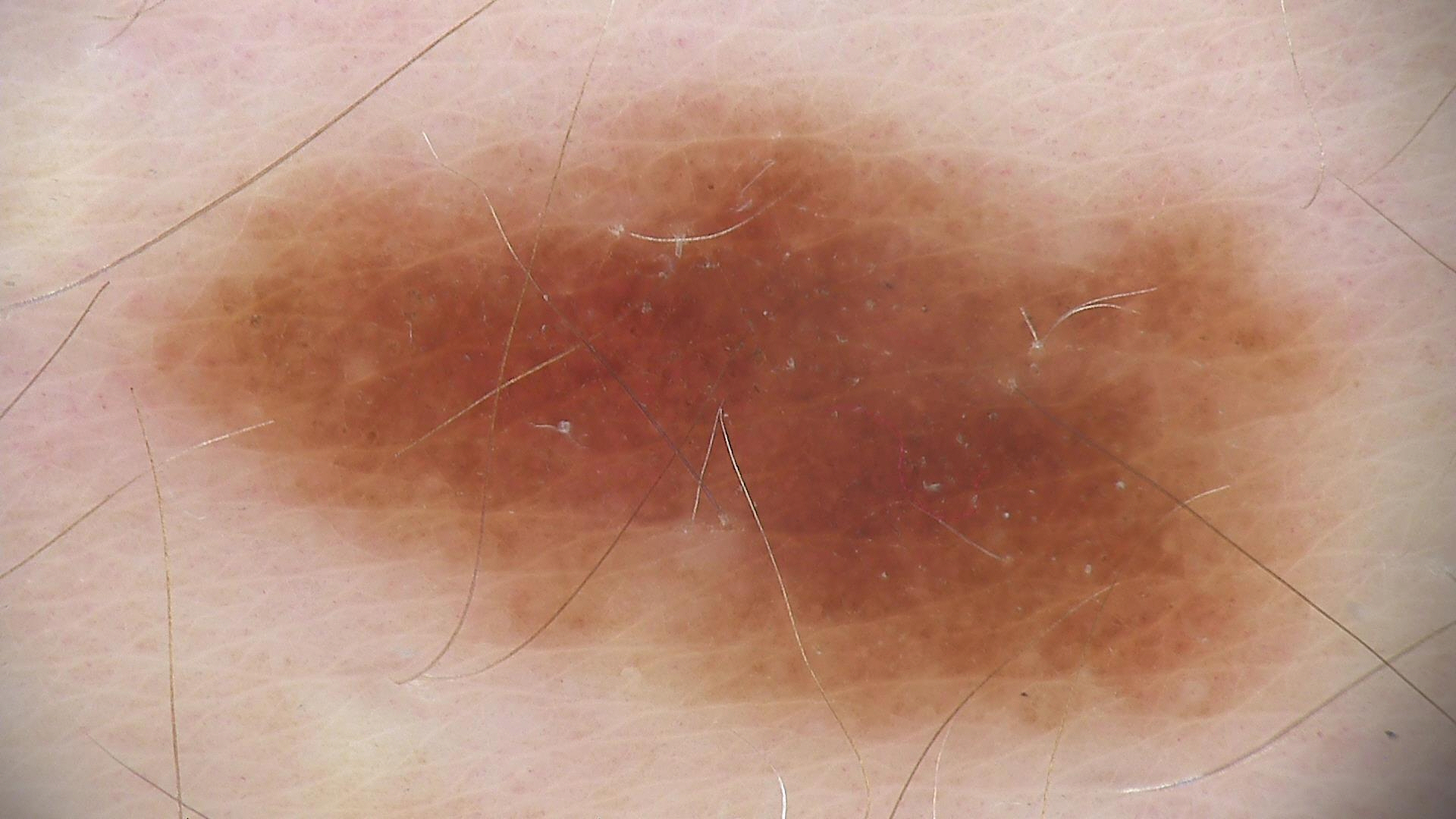The diagnostic label was a dysplastic junctional nevus.